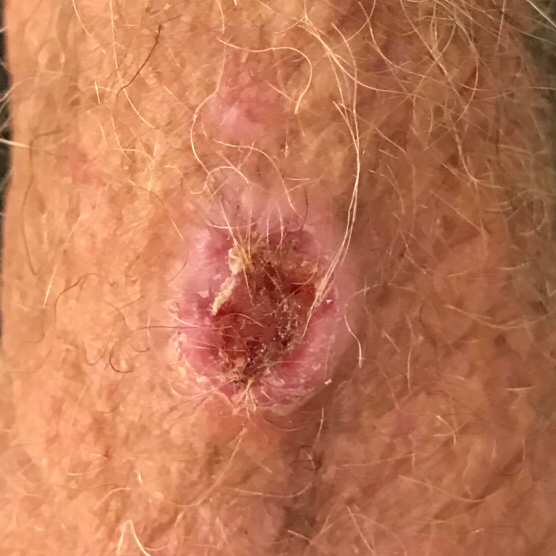imaging = smartphone clinical photo
subject = male, age 74
exposure history = alcohol use, prior skin cancer (patient or family)
skin type = II
location = a forearm
diameter = 20 × 10 mm
patient-reported symptoms = elevation, bleeding, itching, pain
diagnostic label = basal cell carcinoma (biopsy-proven)